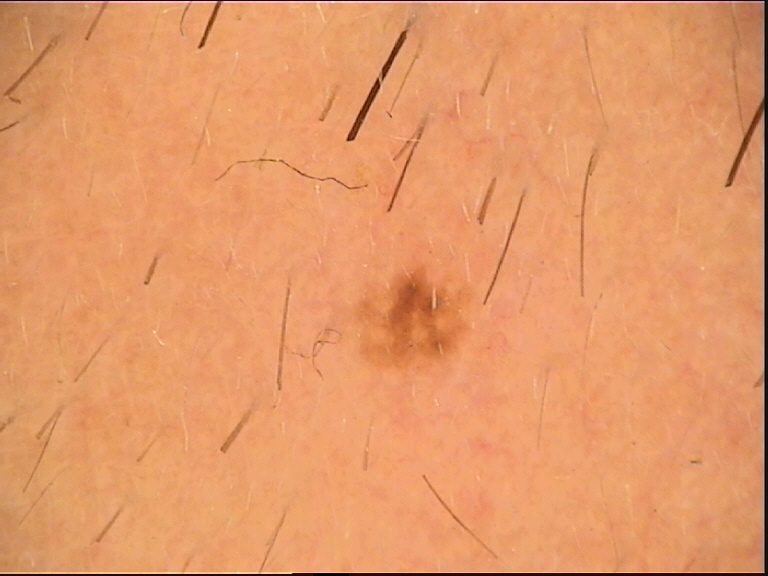Q: What is the imaging modality?
A: dermatoscopy
Q: What is this lesion?
A: dysplastic junctional nevus (expert consensus)